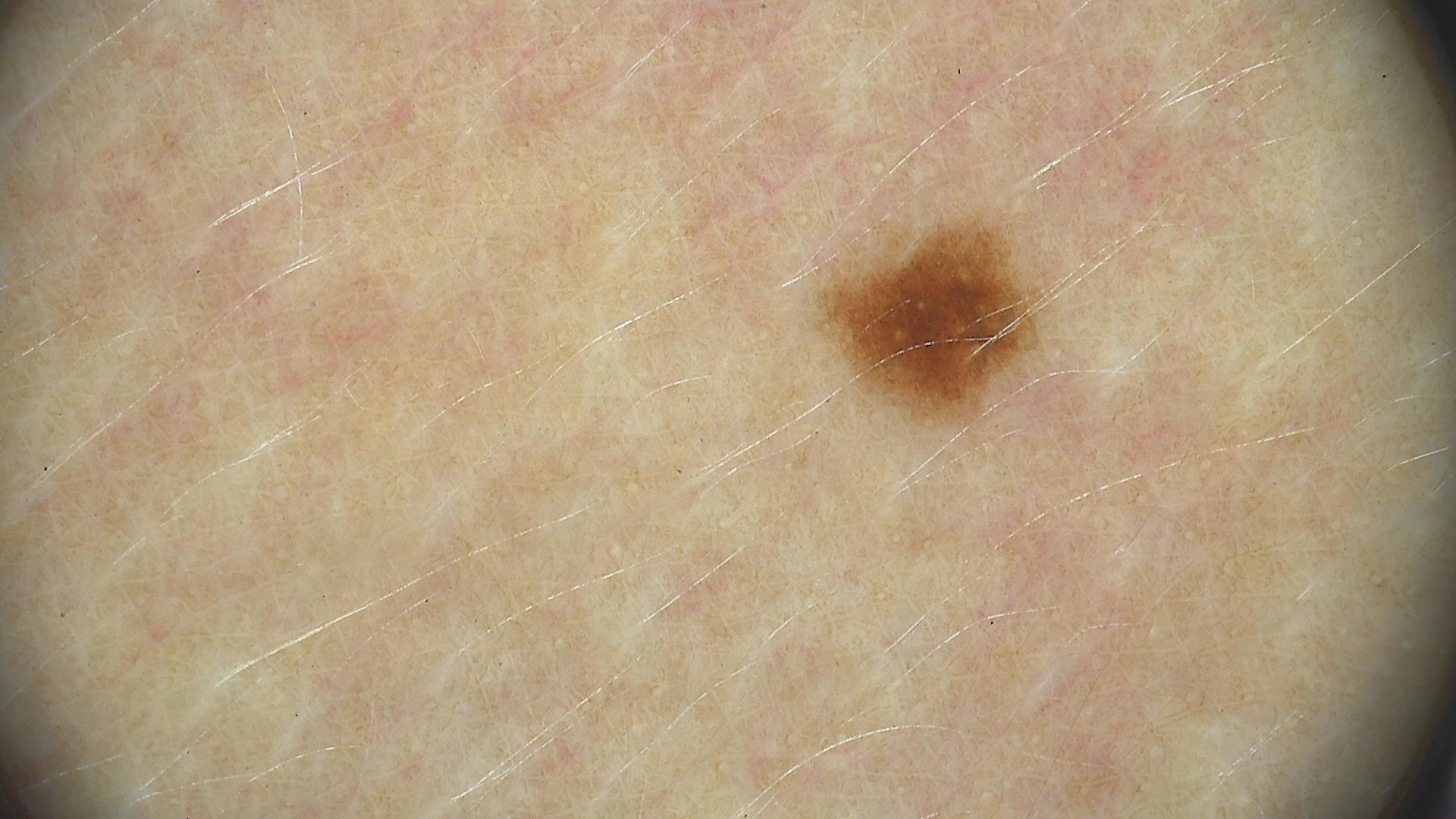The diagnosis was a junctional nevus.